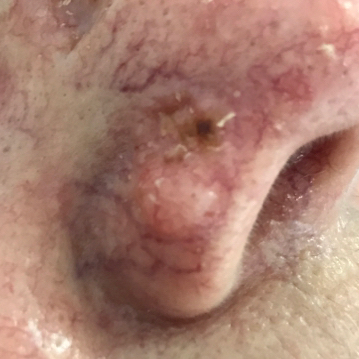A smartphone photograph of a skin lesion. A female subject 66 years old. The lesion is on the nose. The patient describes that the lesion has changed, is elevated, has grown, and has bled. Histopathological examination showed a basal cell carcinoma.